The subject is female · a close-up photograph · the leg is involved.
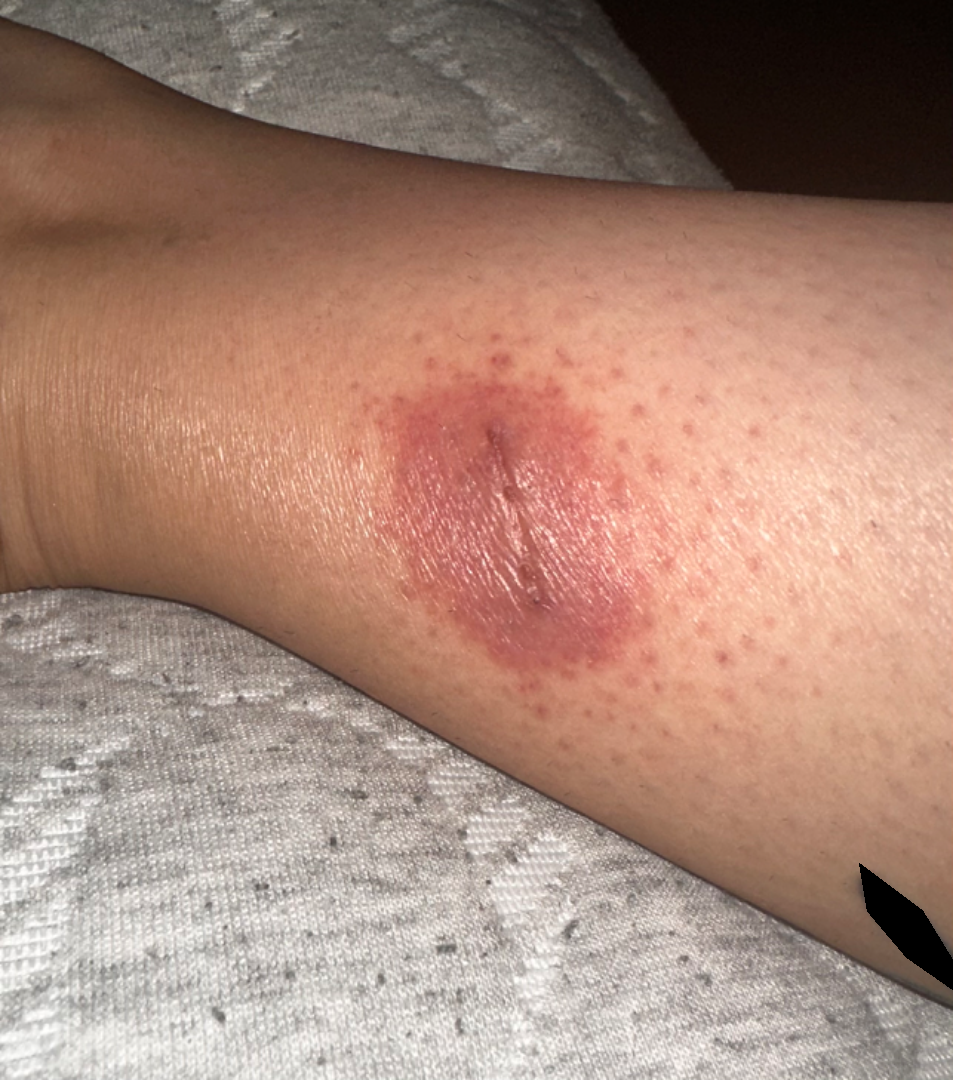On remote review of the image, the favored diagnosis is Allergic Contact Dermatitis; possibly Irritant Contact Dermatitis.